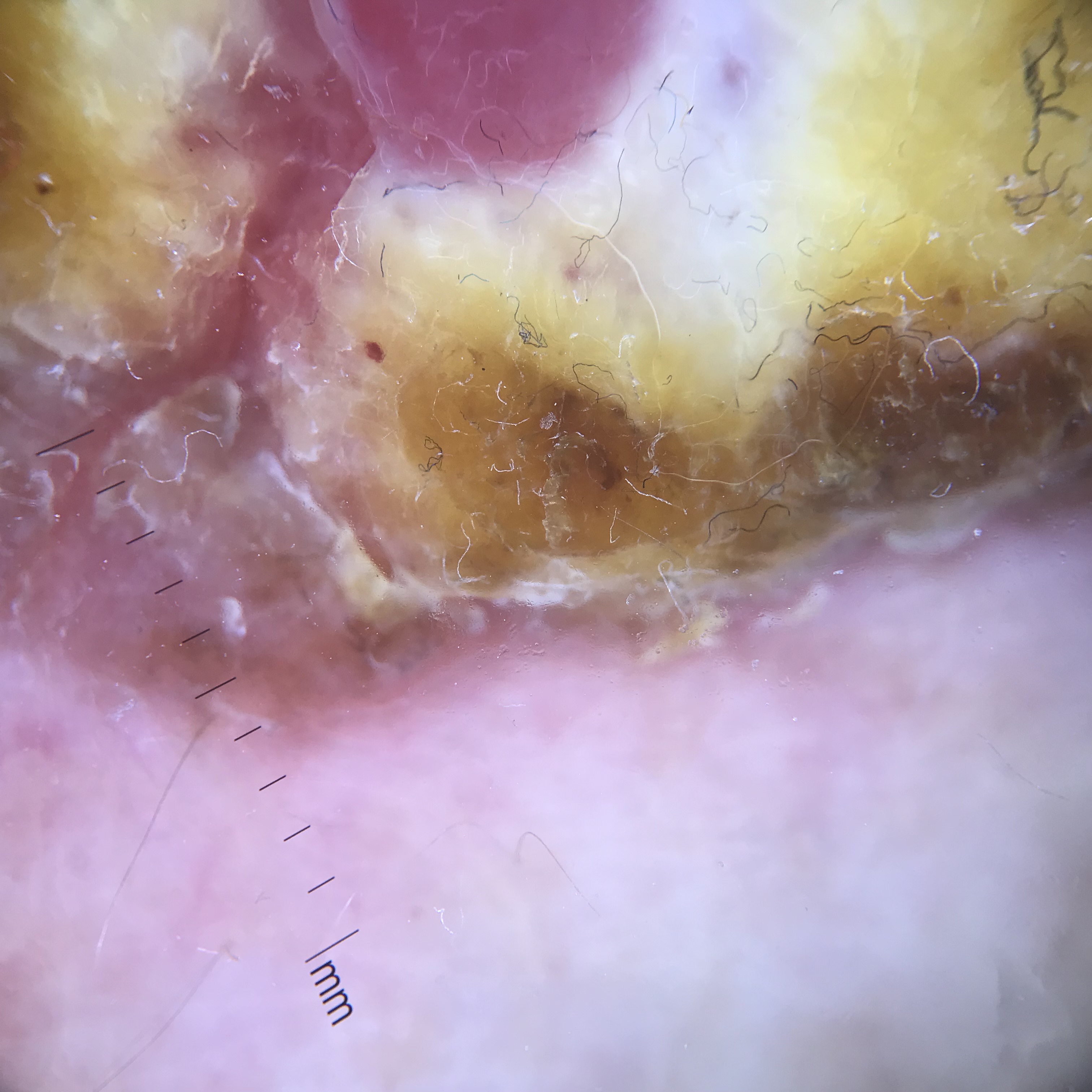image — dermatoscopy | classification — keratinocytic | class — squamous cell carcinoma (biopsy-proven).